The patient notes the lesion is rough or flaky. The patient considered this a rash. Reported duration is one to four weeks. The lesion is associated with enlargement and itching. Located on the arm. The photograph is a close-up of the affected area. Associated systemic symptoms include chills — 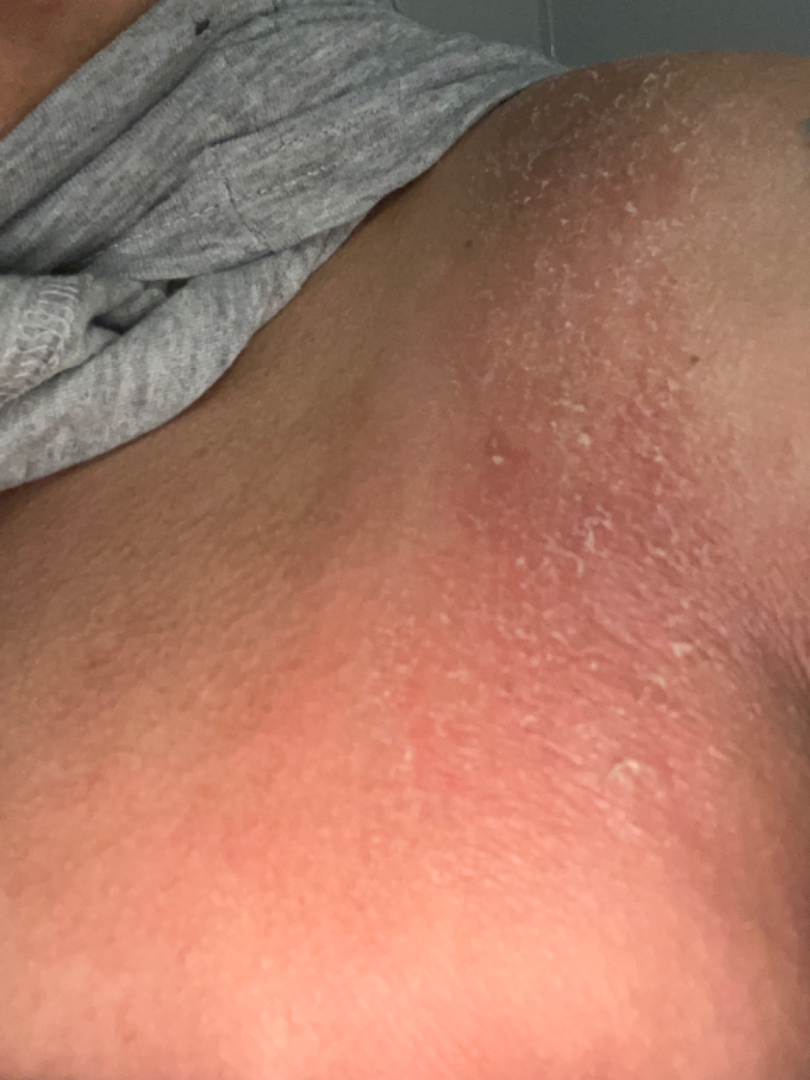differential diagnosis = favoring Drug Rash; also raised was Eczema.